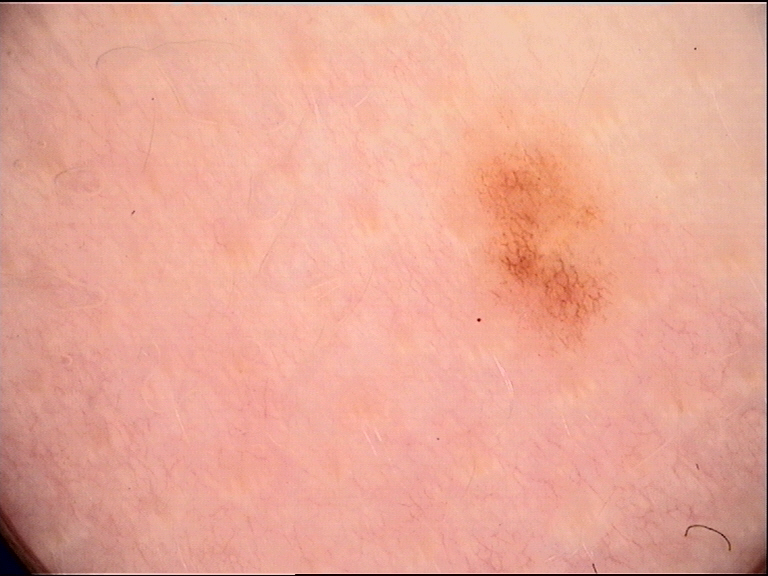Consistent with a dysplastic junctional nevus.